A contact-polarized dermoscopy image of a skin lesion · a male subject aged around 65.
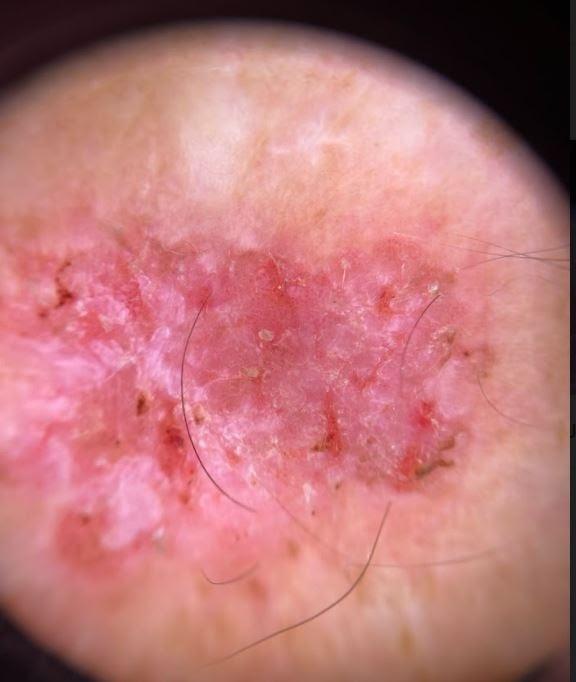body site = an upper extremity
diagnostic label = Squamous cell carcinoma (biopsy-proven)